A close-up photograph — 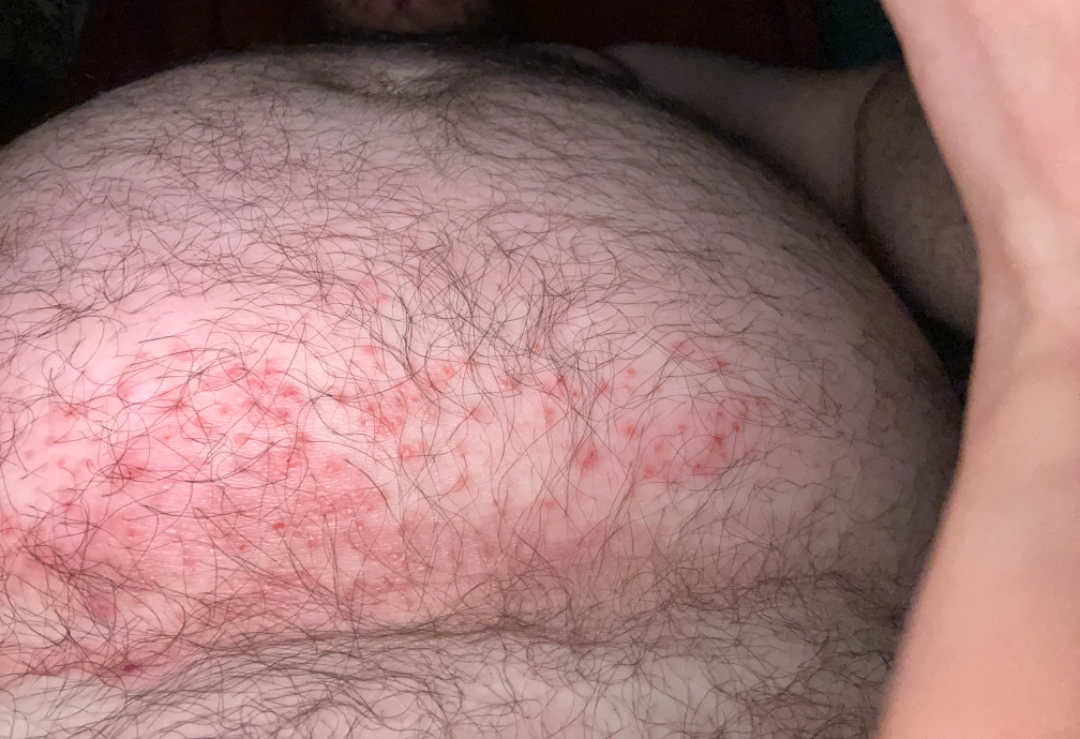Intertrigo and Eczema were considered with similar weight; less probable is Allergic Contact Dermatitis.